A dermatoscopic image of a skin lesion.
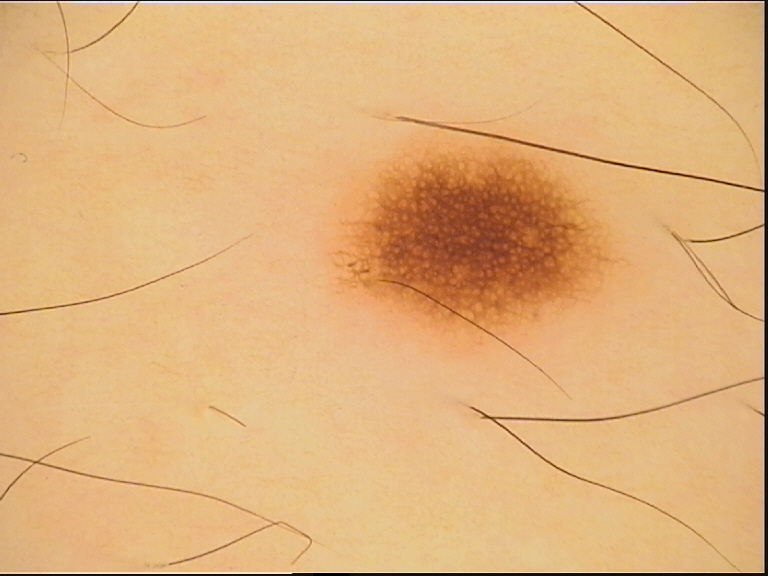The diagnosis was a junctional nevus.